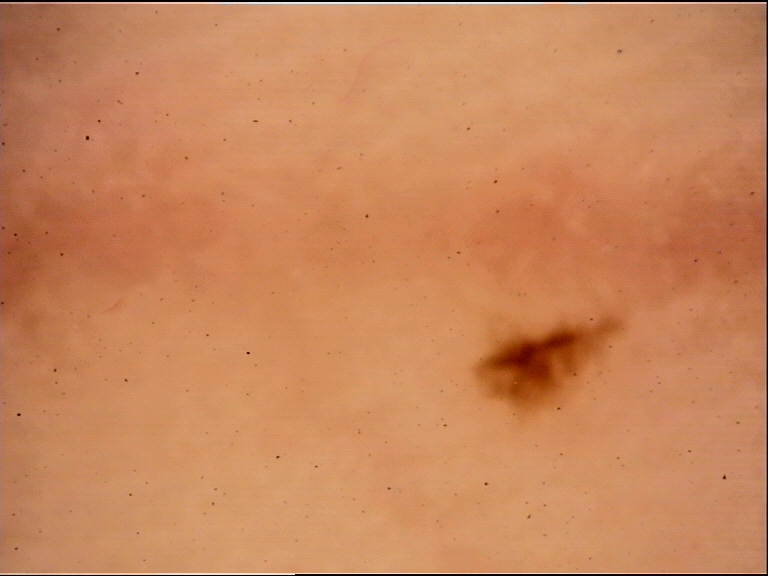Case:
Dermoscopy of a skin lesion.
Conclusion:
Classified as a benign lesion — an acral dysplastic junctional nevus.